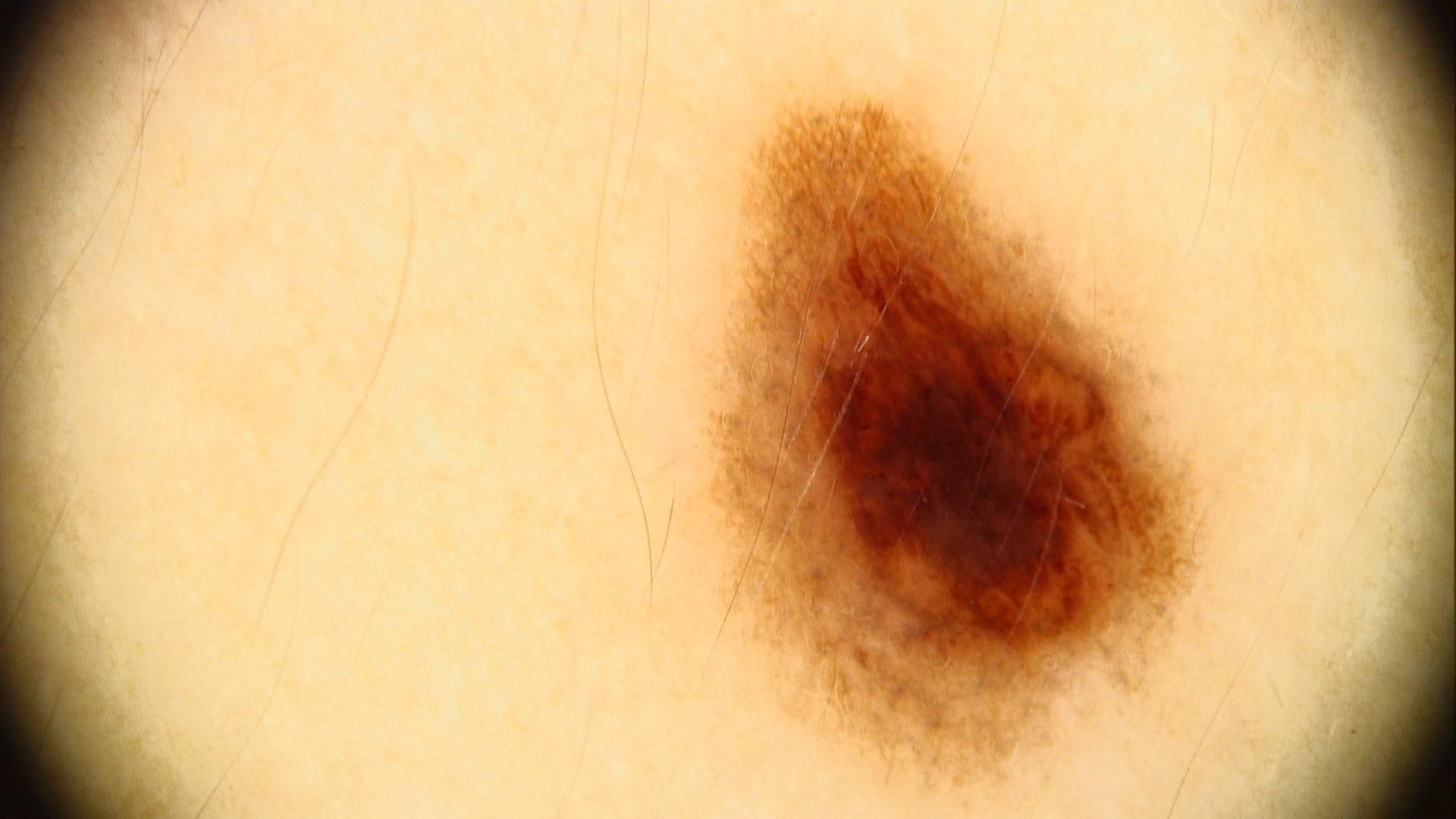| feature | finding |
|---|---|
| impression | Nevus |